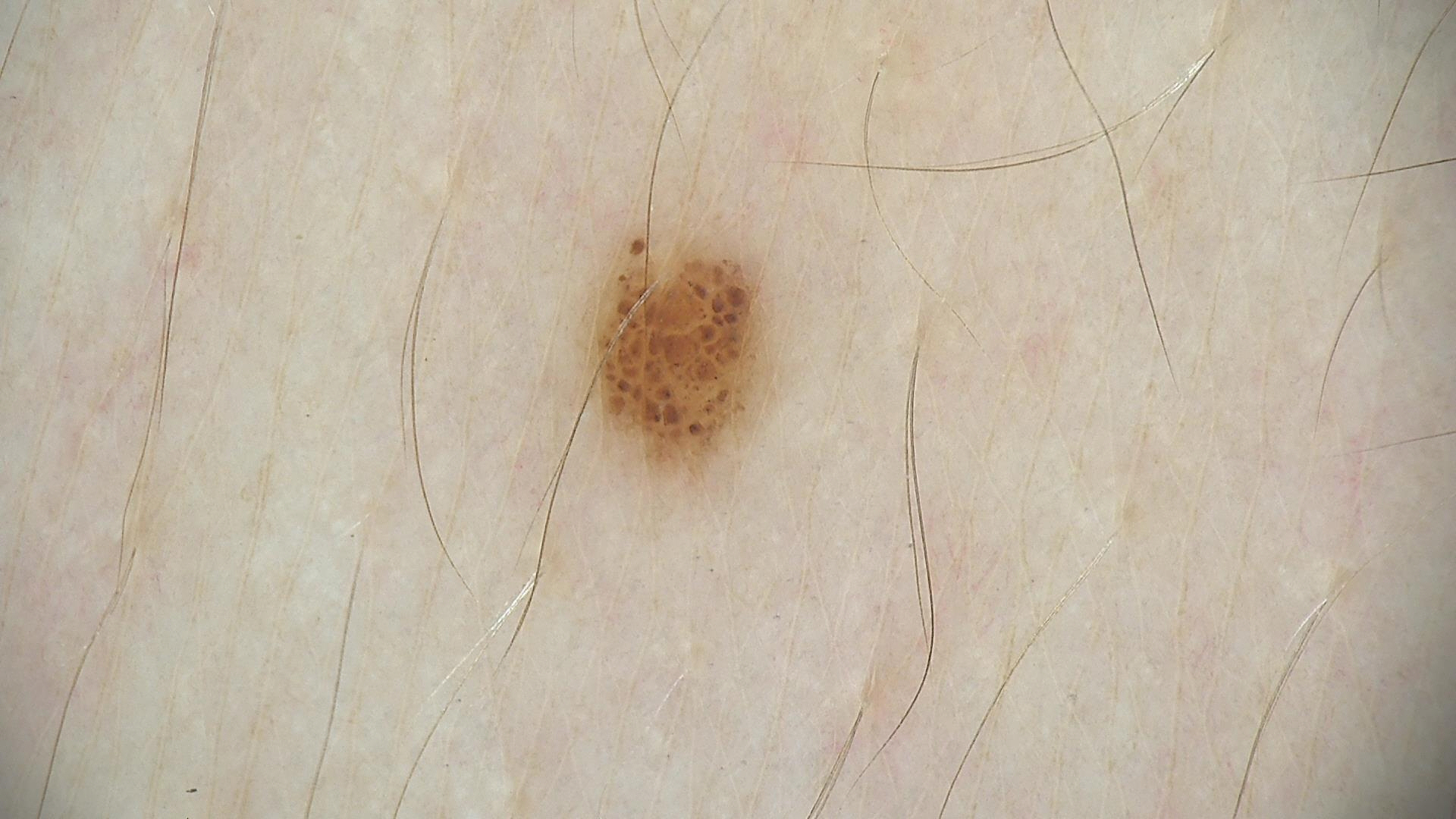| field | value |
|---|---|
| imaging | dermatoscopy |
| classification | banal |
| diagnosis | junctional nevus (expert consensus) |